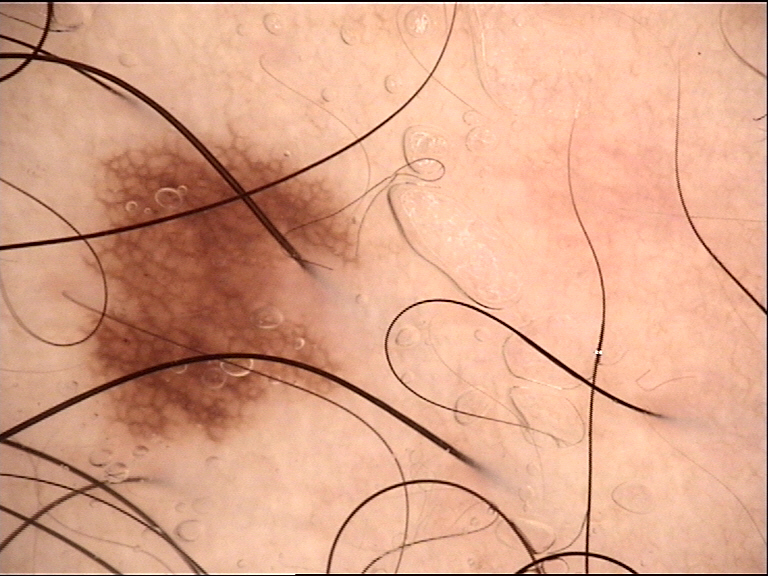assessment = junctional nevus (expert consensus).